Located on the sole of the foot and top or side of the foot · the condition has been present for one to three months · the lesion is described as rough or flaky · the contributor is a female aged 18–29 · the patient notes itching, bothersome appearance and bleeding · this is a close-up image — 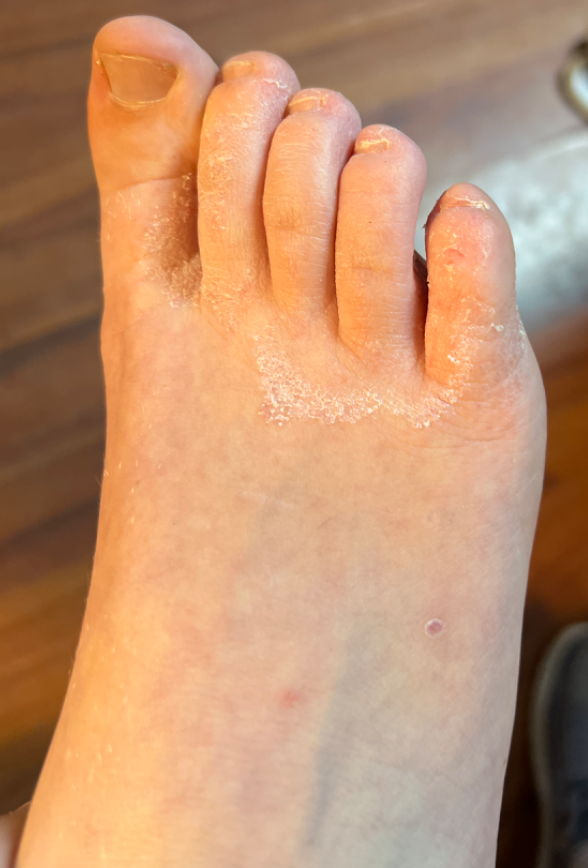The reviewing dermatologists' impression was: favoring Tinea; lower on the differential is Eczema; less probable is Allergic Contact Dermatitis.